Acquired for a research image collection, with no referral diagnosis:
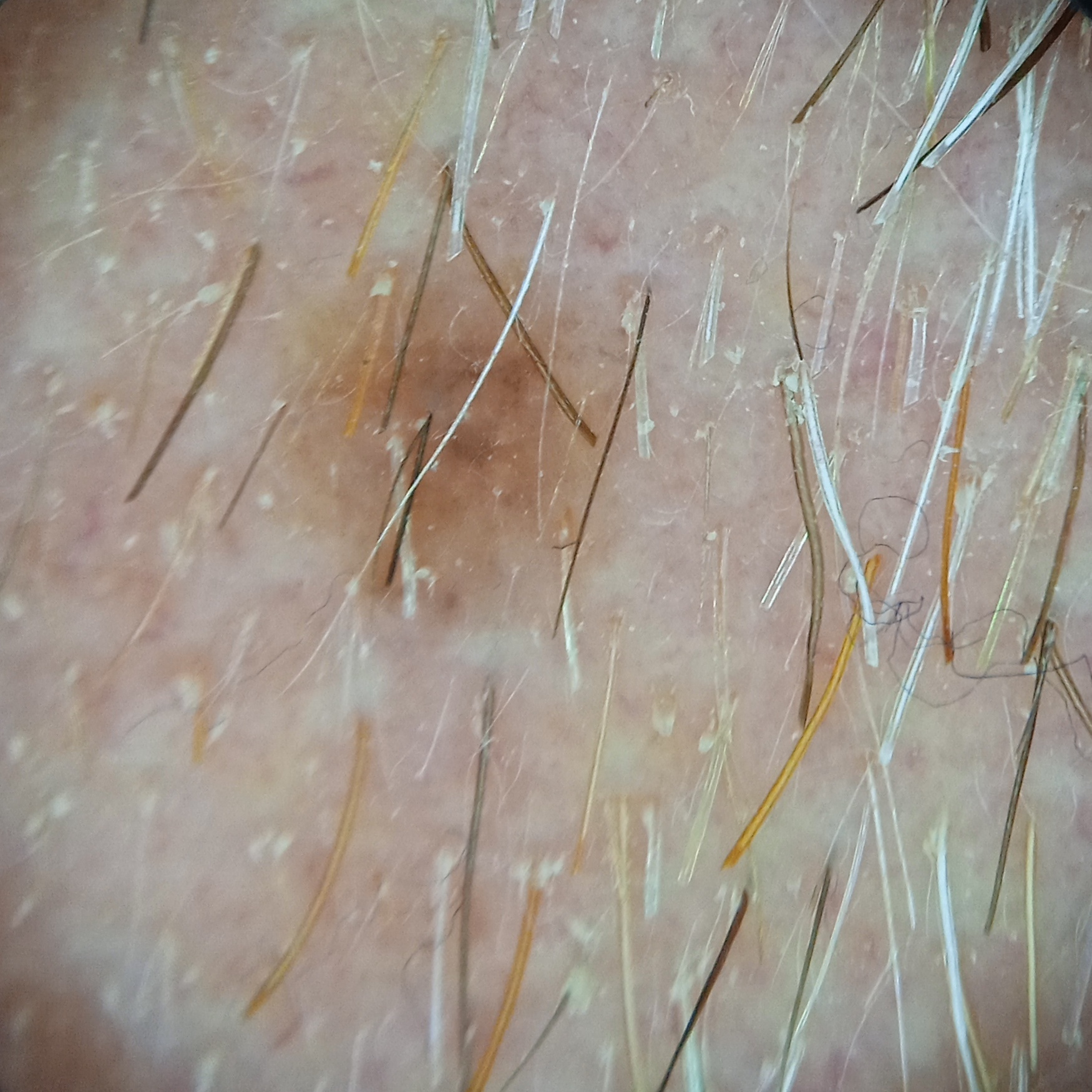The lesion measures approximately 3.7 mm.
The four-dermatologist consensus diagnosis was a melanocytic nevus.